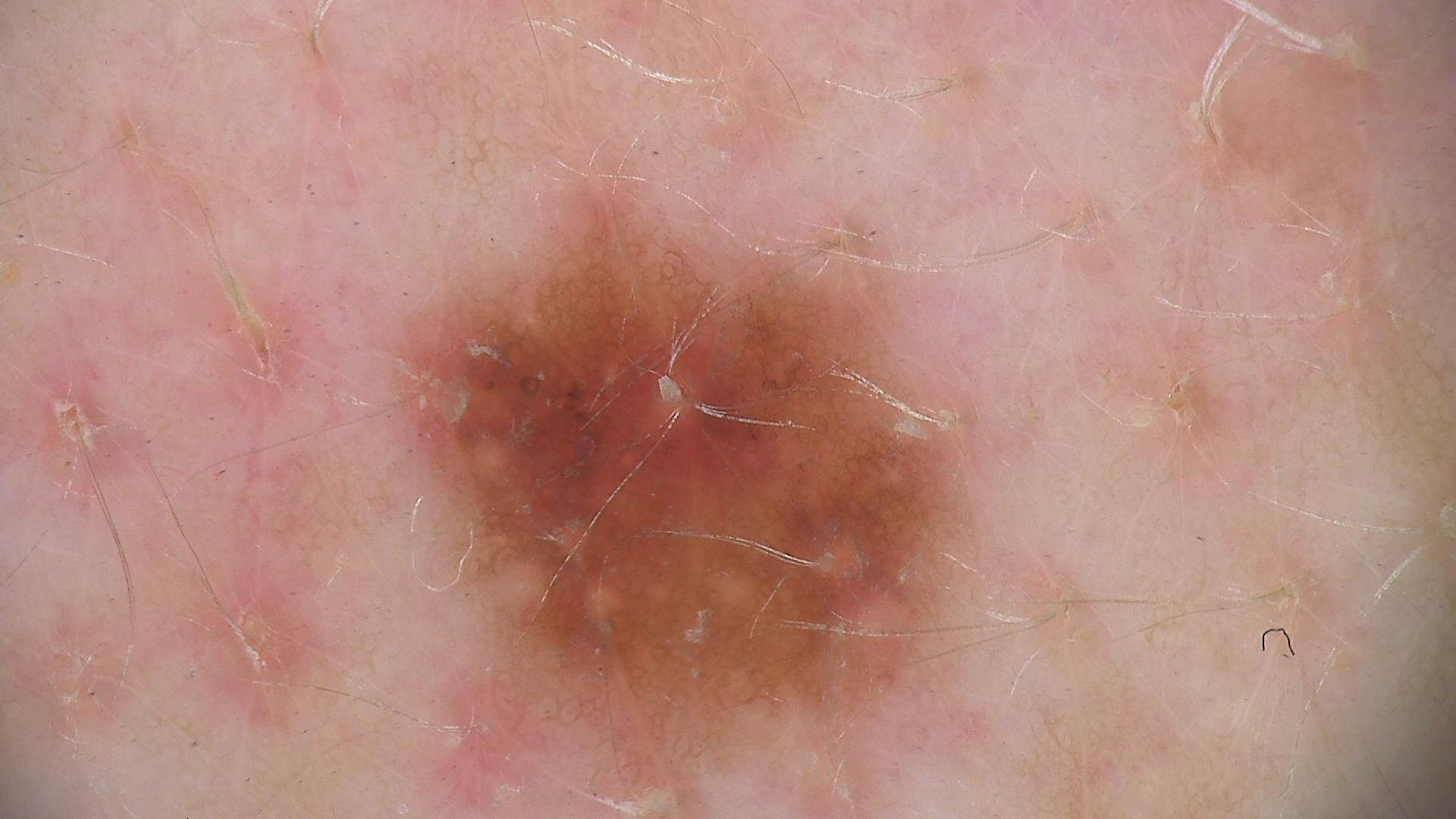<lesion>
<image>dermoscopy</image>
<diagnosis>
<name>dysplastic junctional nevus</name>
<code>jd</code>
<malignancy>benign</malignancy>
<super_class>melanocytic</super_class>
<confirmation>expert consensus</confirmation>
</diagnosis>
</lesion>